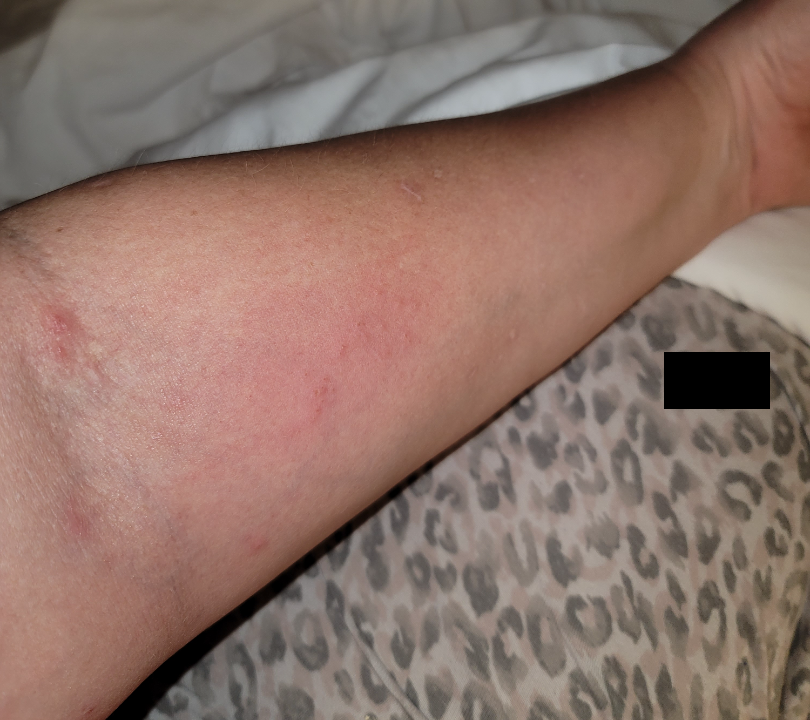Findings: The condition could not be reliably identified from the image. Background: The lesion is associated with enlargement and itching. The contributor reports the lesion is flat. Present for about one day. Self-categorized by the patient as skin that appeared healthy to them. This image was taken at a distance. The lesion involves the arm.